A dermoscopic photograph of a skin lesion:
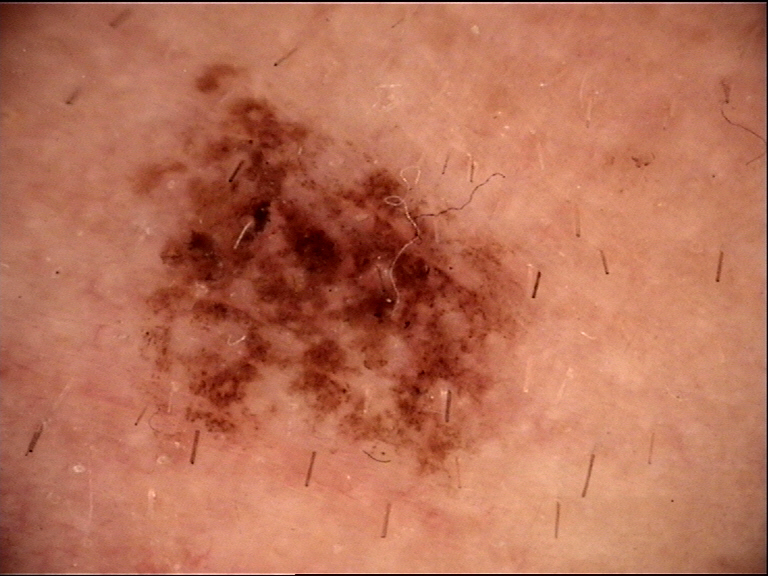classification: banal, diagnostic label: congenital compound nevus (expert consensus).